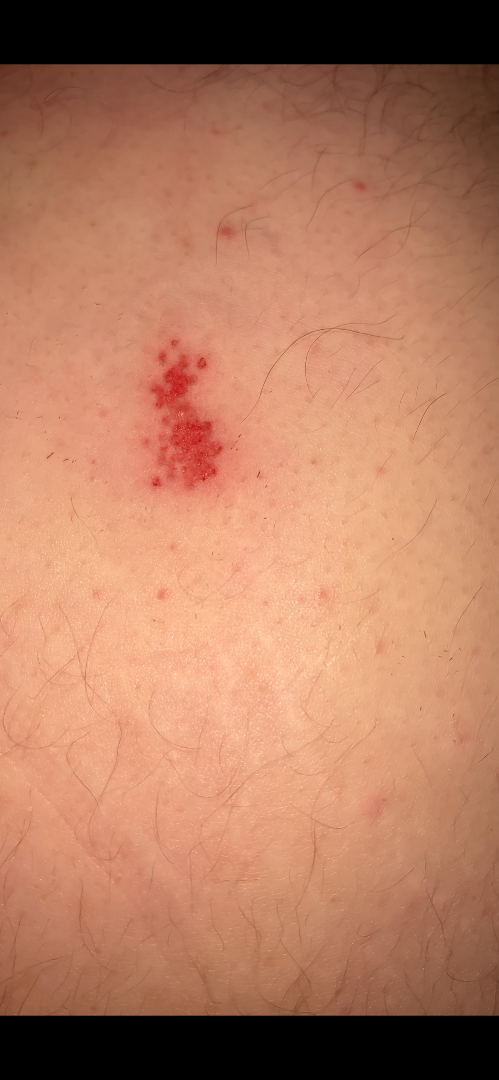{
  "differential": {
    "tied_lead": [
      "Herpes Zoster",
      "Herpes Simplex"
    ]
  }
}